The patient is a female aged around 30 · a skin lesion imaged with a dermatoscope — 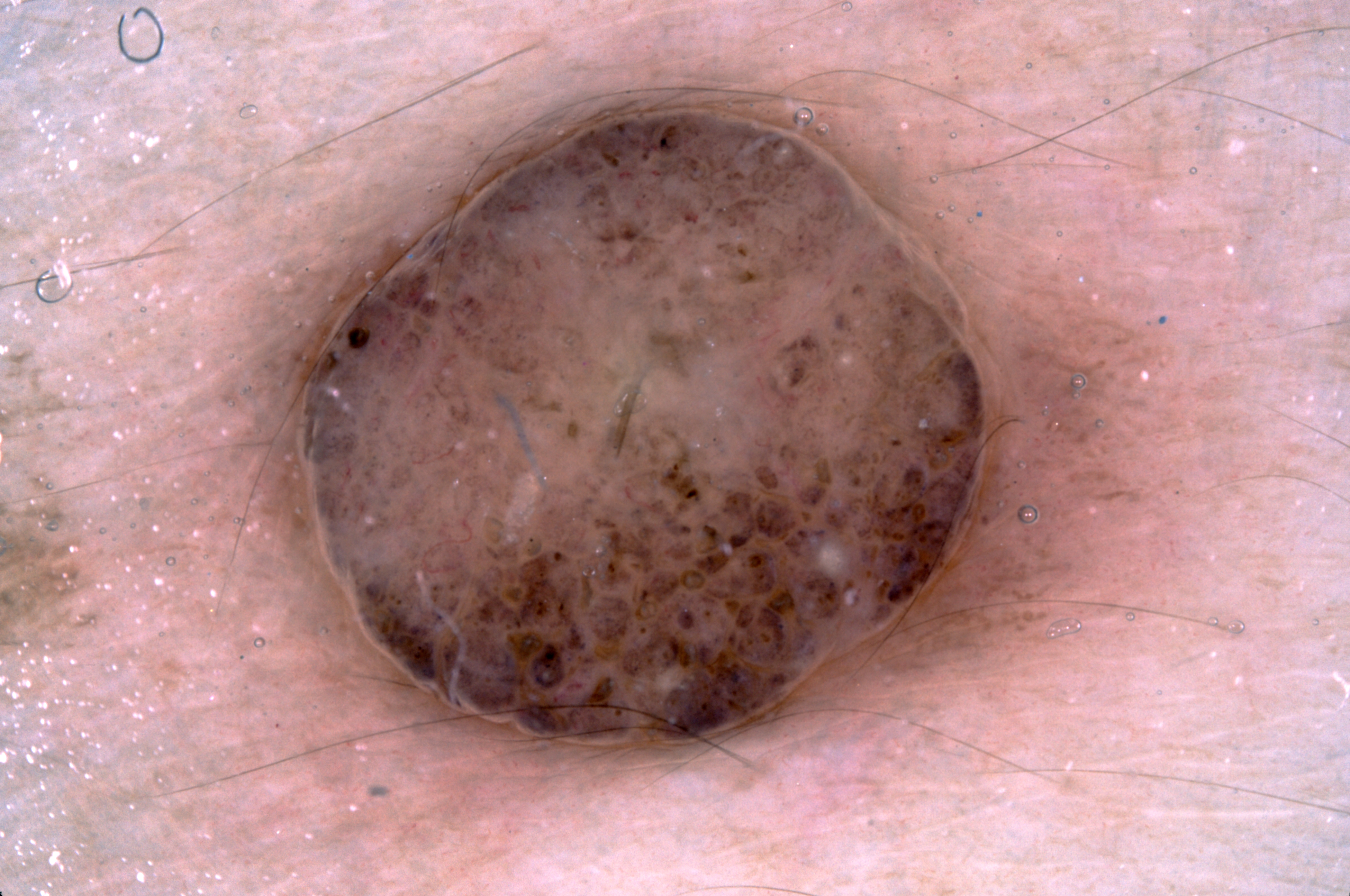Findings:
A prominent lesion filling much of the field. In (x1, y1, x2, y2) order, the lesion is bounded by bbox=[221, 70, 1139, 785]. The dermoscopic pattern shows milia-like cysts; no negative network, pigment network, or streaks.
Conclusion:
Consistent with a melanocytic nevus.